Dermoscopy of a skin lesion.
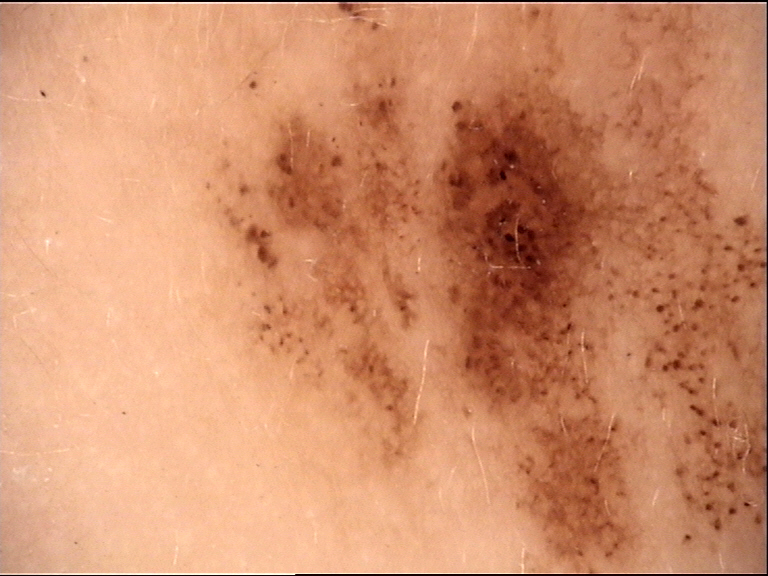The diagnosis was a banal lesion — a congenital junctional nevus.